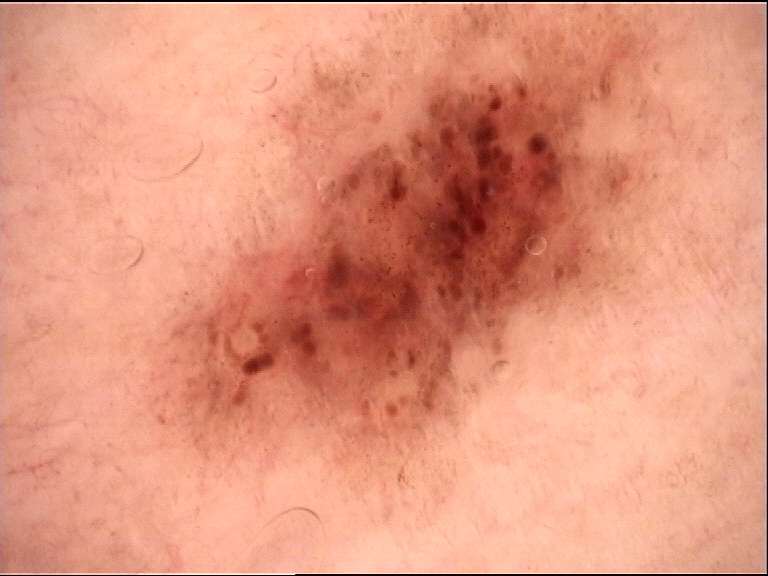Q: What kind of image is this?
A: dermatoscopy
Q: What was the diagnostic impression?
A: dysplastic compound nevus (expert consensus)